The patient reports the lesion is raised or bumpy and rough or flaky. The subject is a female aged 60–69. The affected area is the back of the hand, leg and top or side of the foot. This image was taken at an angle. The patient considered this a rash. The patient reported no systemic symptoms. The condition has been present for one to four weeks. Fitzpatrick skin type I. Symptoms reported: bothersome appearance: 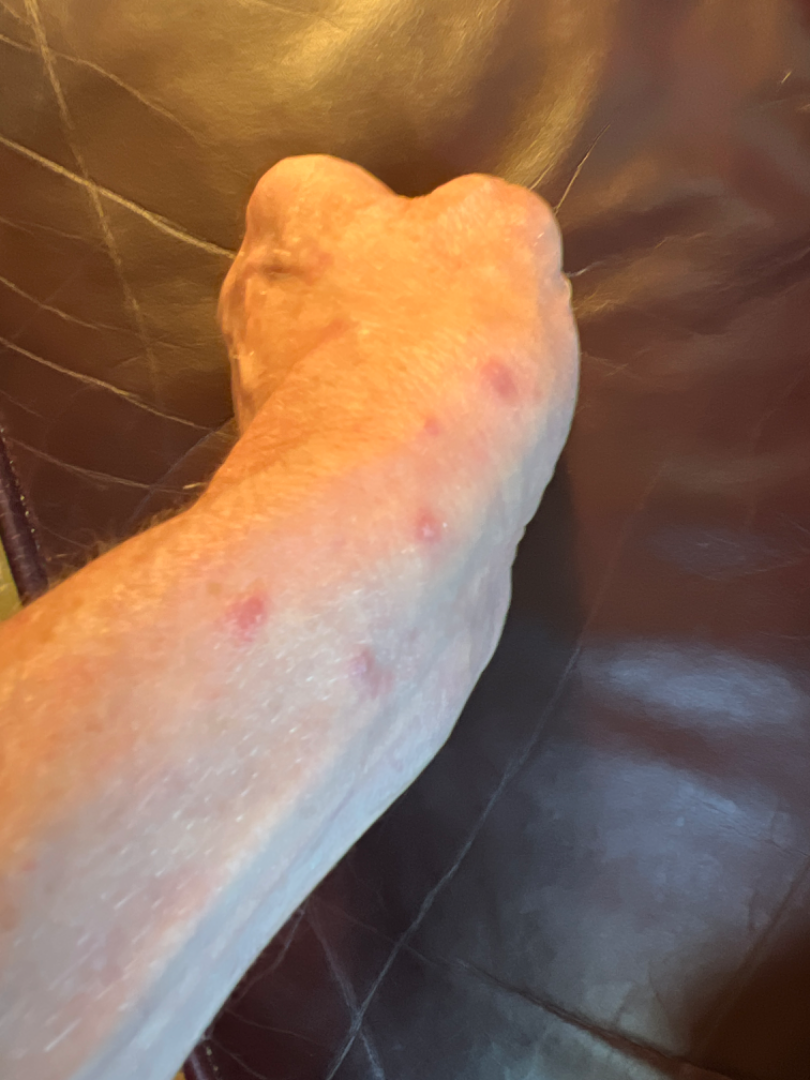<case>
<differential>
  <leading>Impetigo</leading>
  <considered>Skin infection, Lichen planus/lichenoid eruption</considered>
</differential>
</case>